No associated systemic symptoms reported · the lesion is described as raised or bumpy and rough or flaky · the photograph is a close-up of the affected area · female subject, age 70–79 · the lesion involves the front of the torso · the patient considered this skin that appeared healthy to them: 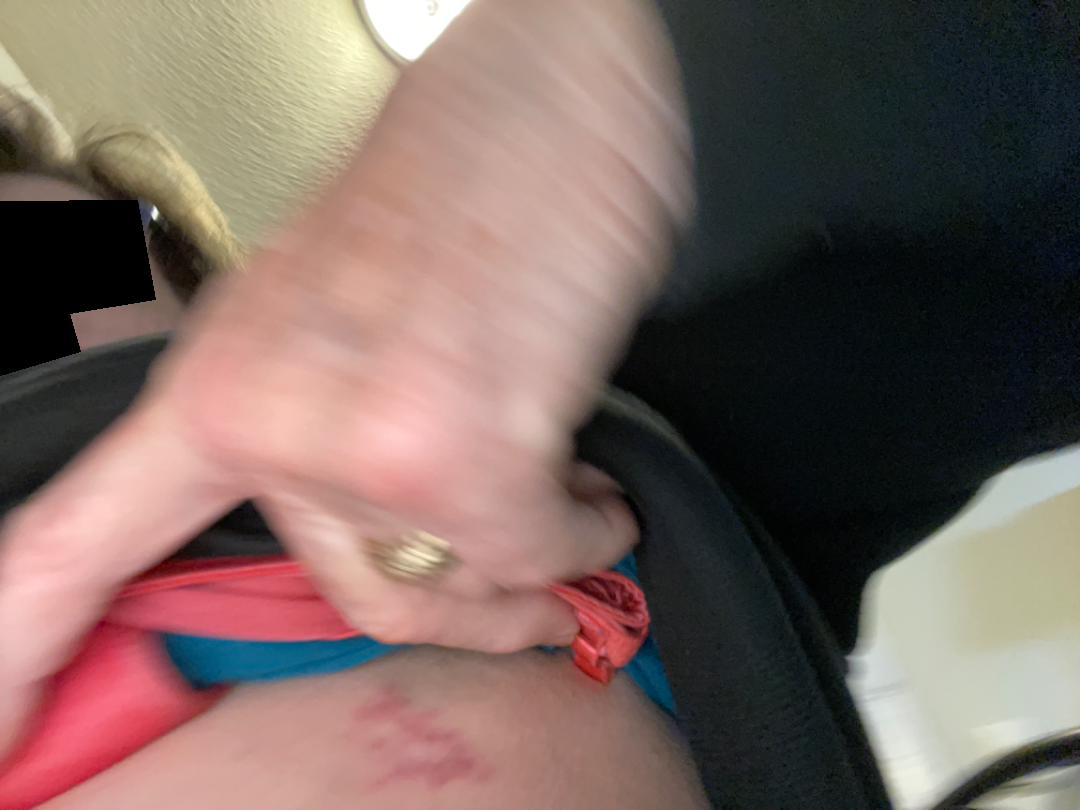<summary>
<assessment>ungradable on photographic review</assessment>
</summary>